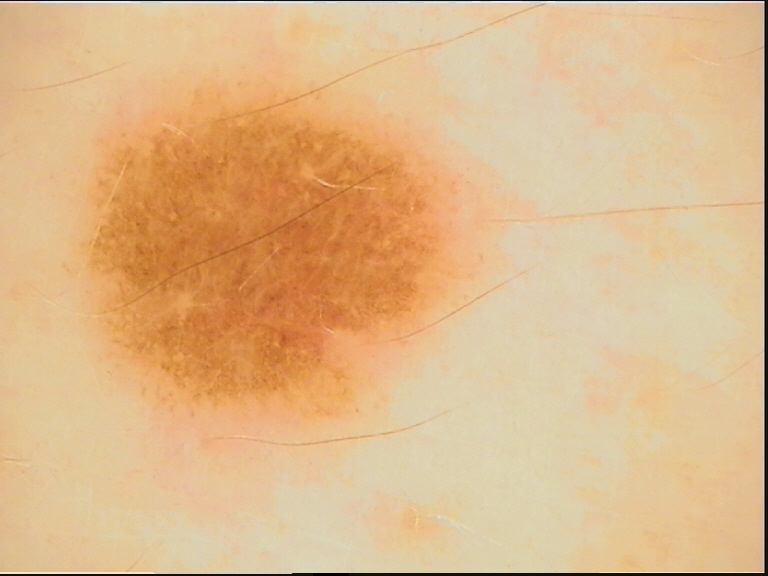class: dysplastic junctional nevus (expert consensus).